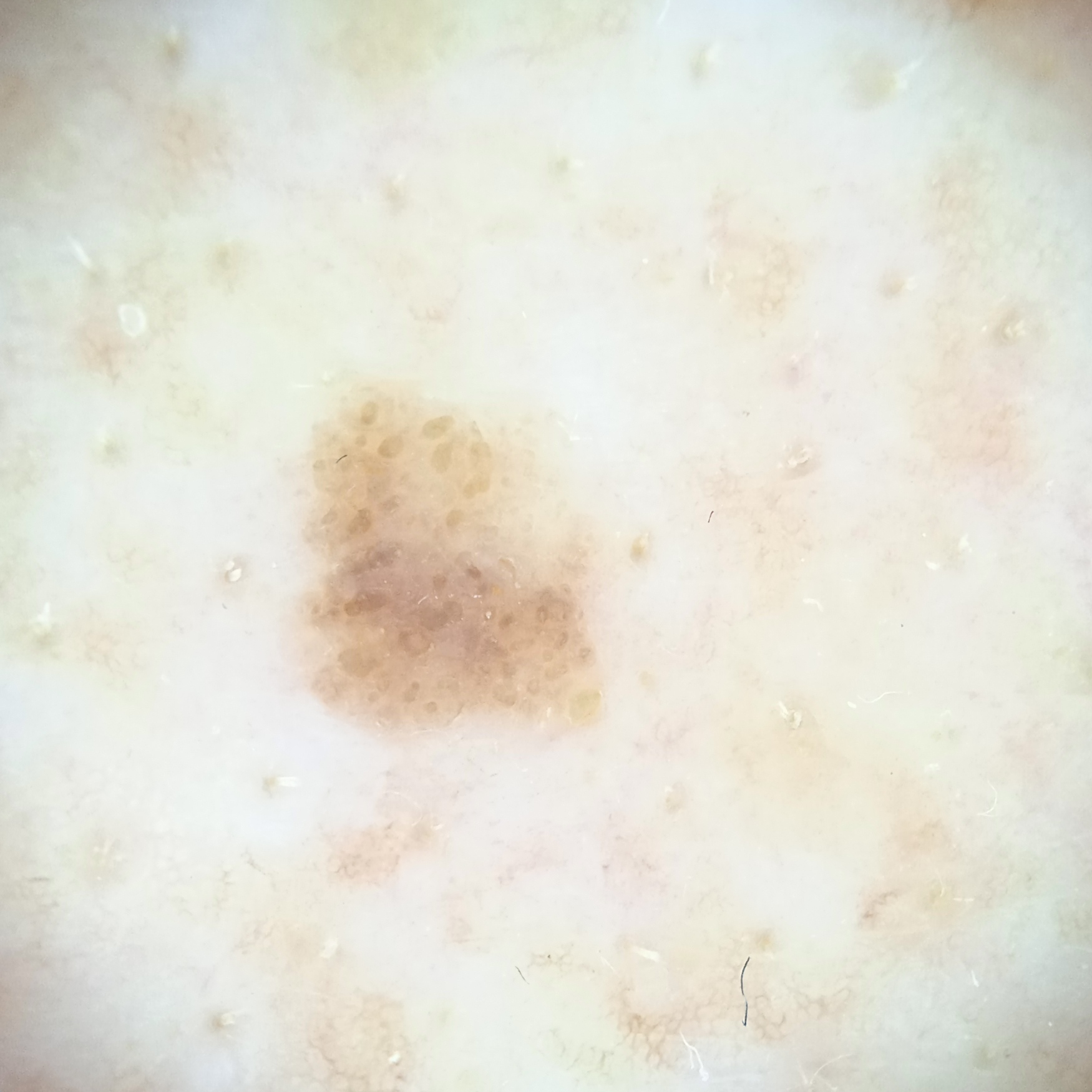{
  "referral": "research study (no referral diagnosis)",
  "patient": {
    "age": 66,
    "sex": "male"
  },
  "image": "dermoscopy",
  "lesion_location": "the back",
  "lesion_size": {
    "diameter_mm": 4.5
  },
  "diagnosis": {
    "name": "seborrheic keratosis",
    "malignancy": "benign"
  }
}